A clinical photo of a skin lesion taken with a smartphone.
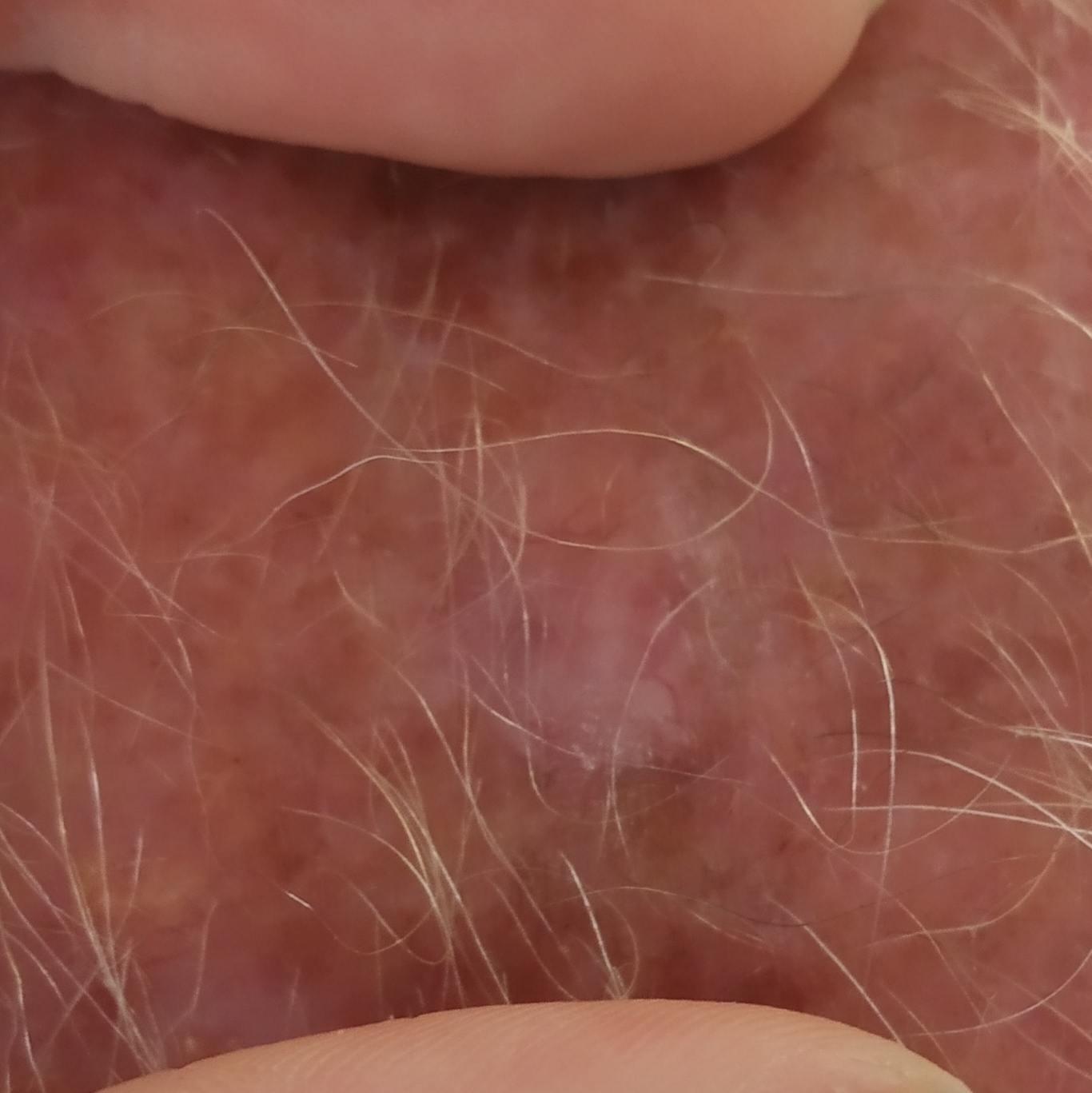<lesion>
  <lesion_location>a forearm</lesion_location>
  <symptoms>
    <present>elevation, itching</present>
    <absent>bleeding, pain</absent>
  </symptoms>
  <diagnosis>
    <name>basal cell carcinoma</name>
    <code>BCC</code>
    <malignancy>malignant</malignancy>
    <confirmation>histopathology</confirmation>
  </diagnosis>
</lesion>